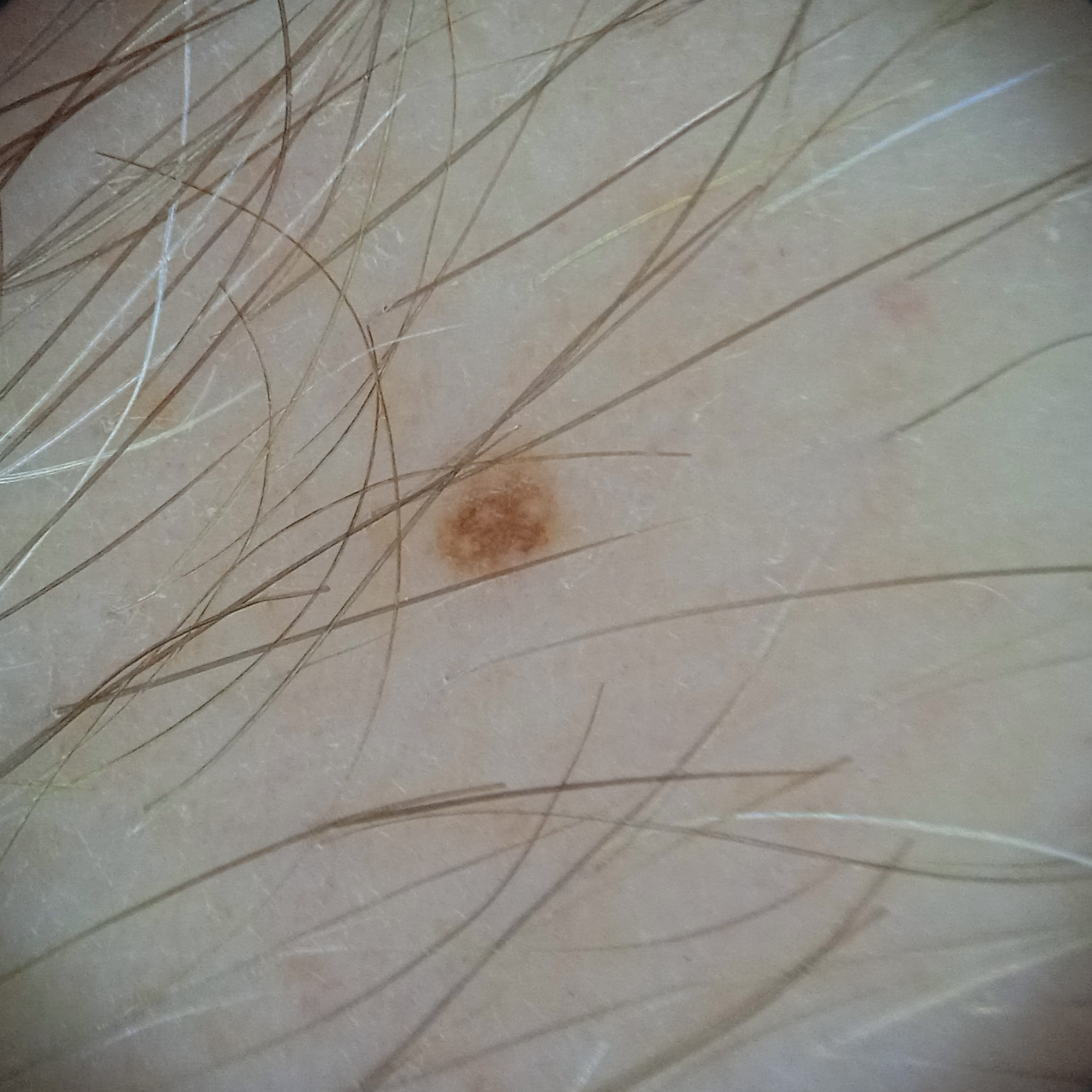{"image": "dermatoscopic image", "referral": "research study (no referral diagnosis)", "sun_reaction": "skin reddens with sun exposure", "lesion_location": "an arm", "lesion_size": {"diameter_mm": 1.5}, "diagnosis": {"name": "melanocytic nevus", "malignancy": "benign"}}